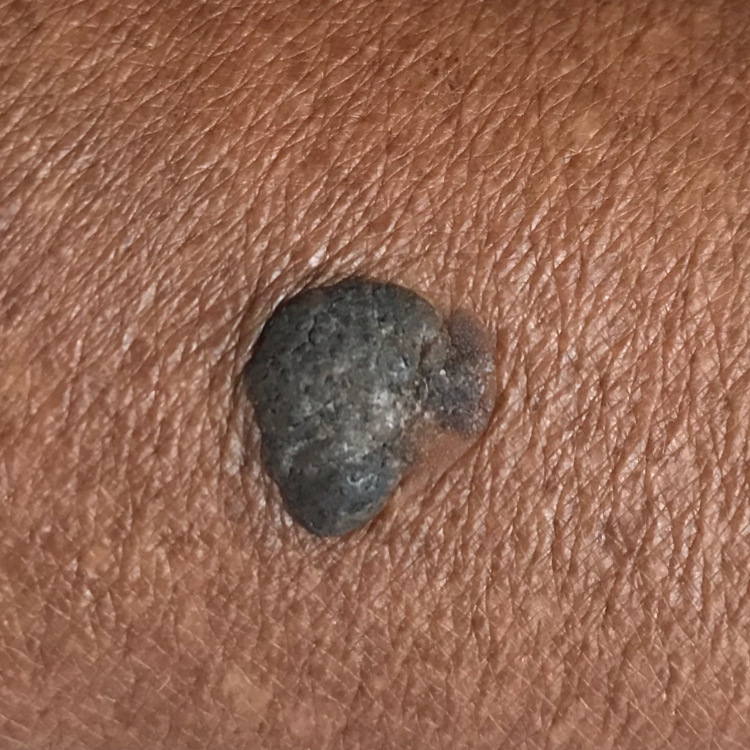patient:
  age: 73
image: clinical photograph
symptoms:
  present:
    - elevation
    - growth
diagnosis:
  name: seborrheic keratosis
  code: SEK
  malignancy: benign
  confirmation: clinical consensus